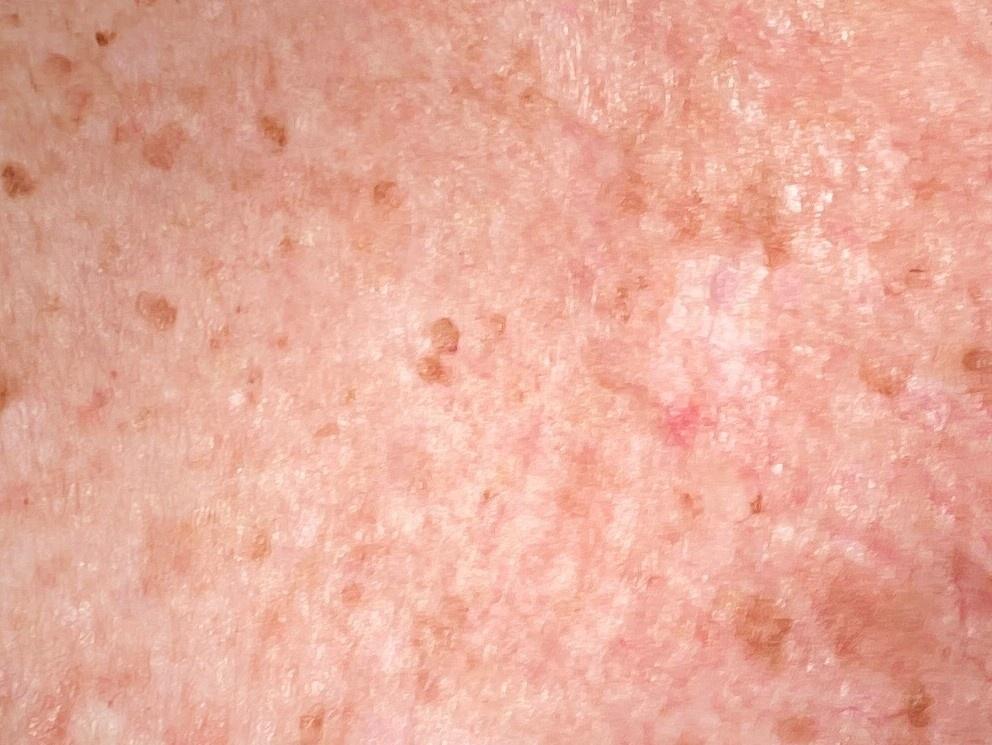relevant background: a previous melanoma | subject: female, approximately 75 years of age | body site: the trunk | diagnosis: Squamous cell carcinoma (biopsy-proven).